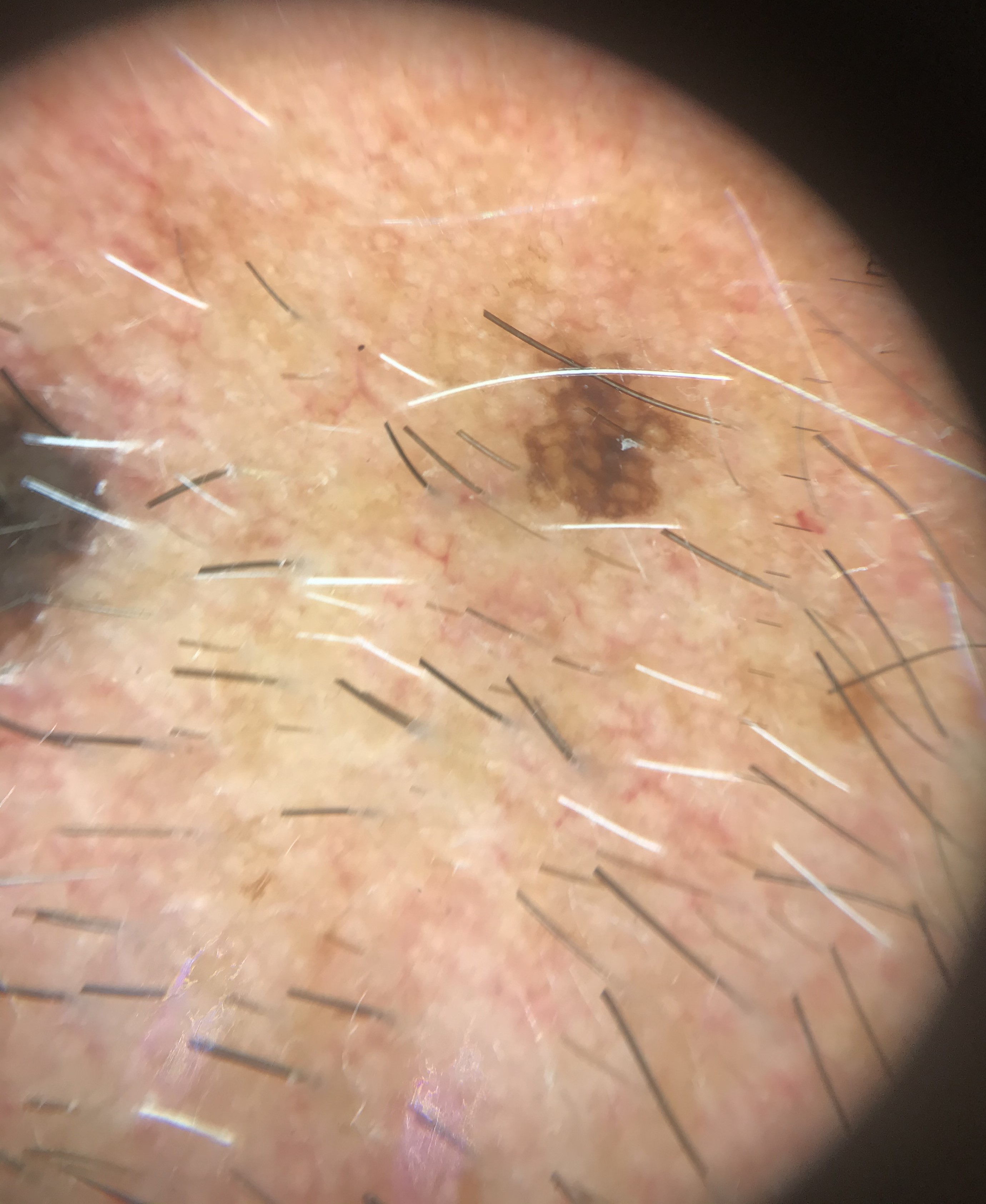The architecture is that of a keratinocytic lesion. Labeled as a seborrheic keratosis.